A female subject aged 23-27 · dermoscopy of a skin lesion — 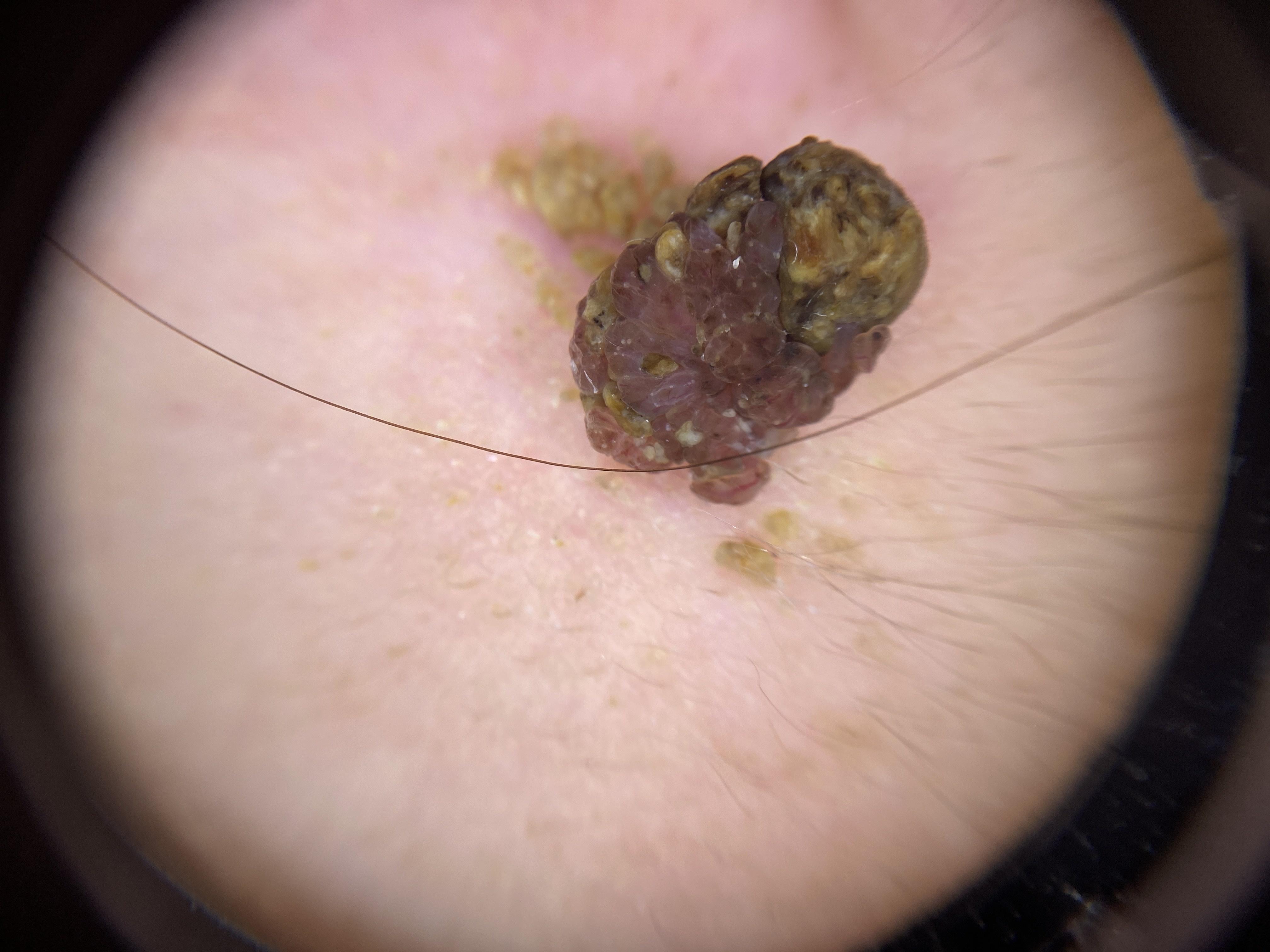Q: Where on the body is the lesion?
A: the head or neck
Q: What was the clinical impression?
A: Nevus